The subject is a female aged 60–69. Located on the leg. This image was taken at an angle:
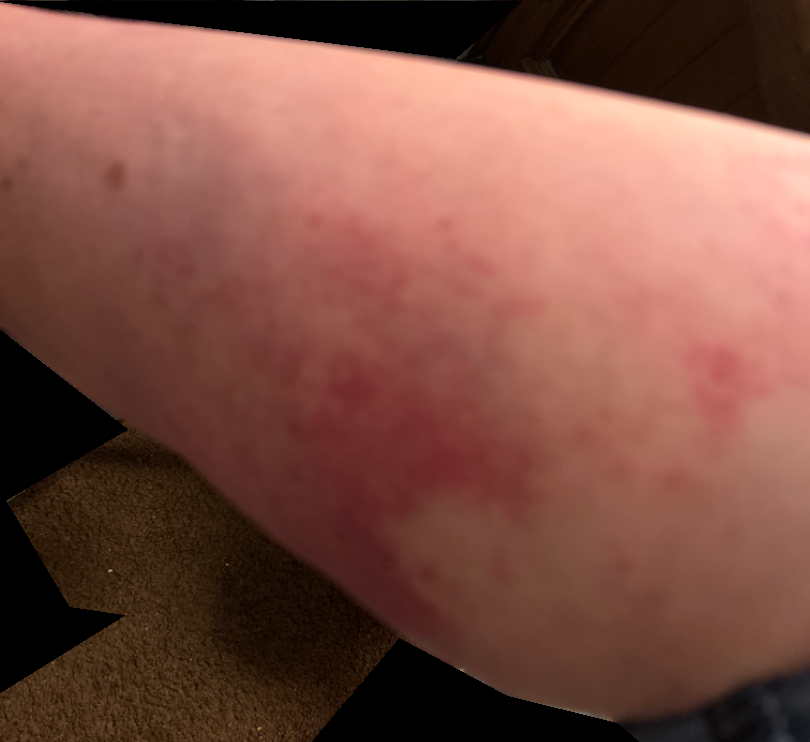symptom duration = less than one week
symptoms = darkening, itching, pain and enlargement
constitutional symptoms = joint pain and shortness of breath
described texture = flat
clinical impression = a single dermatologist reviewed the case: in keeping with Leukocytoclastic Vasculitis